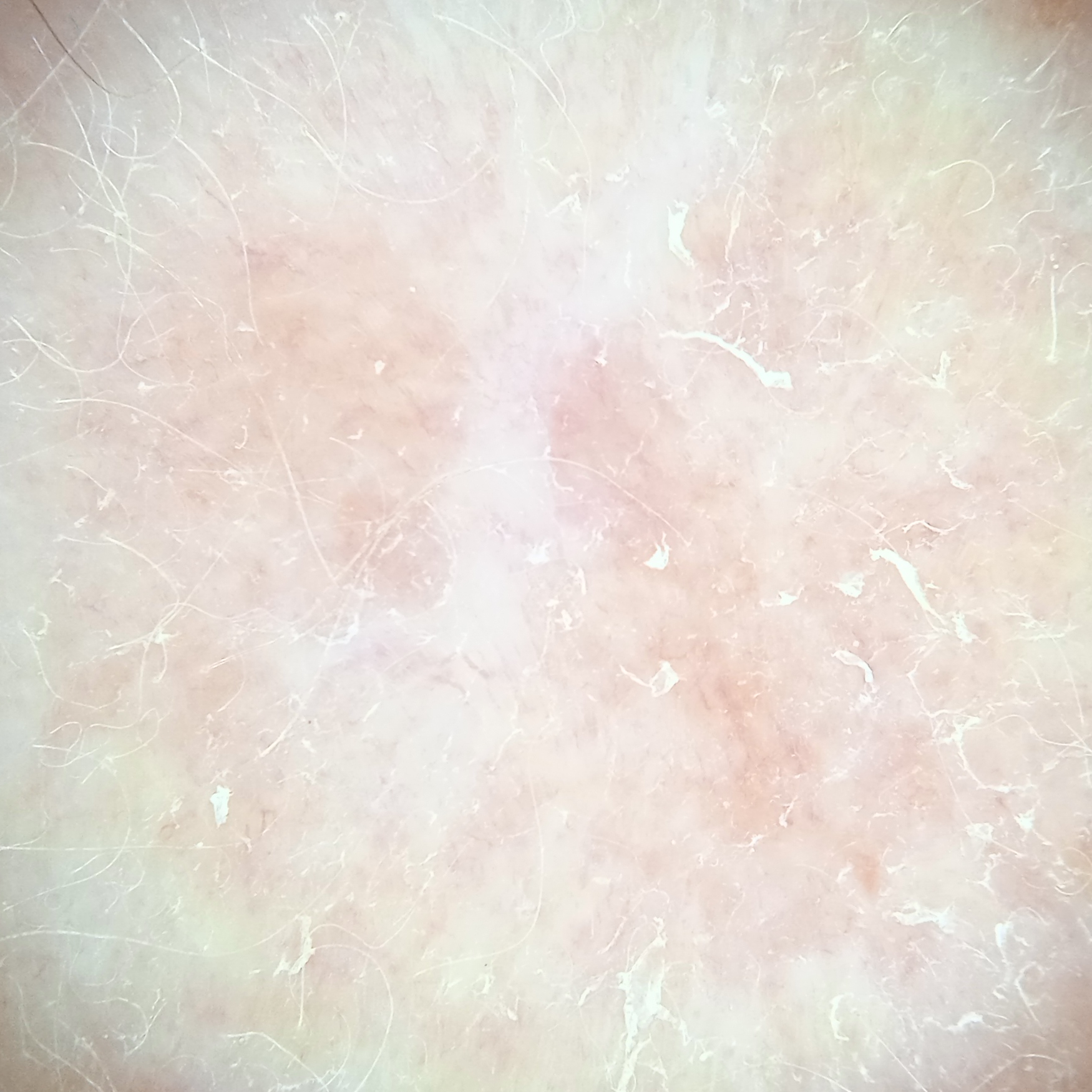Diagnosis: Confirmed on histopathology as a basal cell carcinoma, following excision, with tumor thickness 2.6 mm.